The patient notes the lesion is flat and rough or flaky. No relevant systemic symptoms. Reported lesion symptoms include itching, enlargement and bothersome appearance. The subject is 60–69, female. The patient considered this a rash. Present for more than one year. The lesion involves the back of the torso, top or side of the foot, leg and arm. Close-up view — 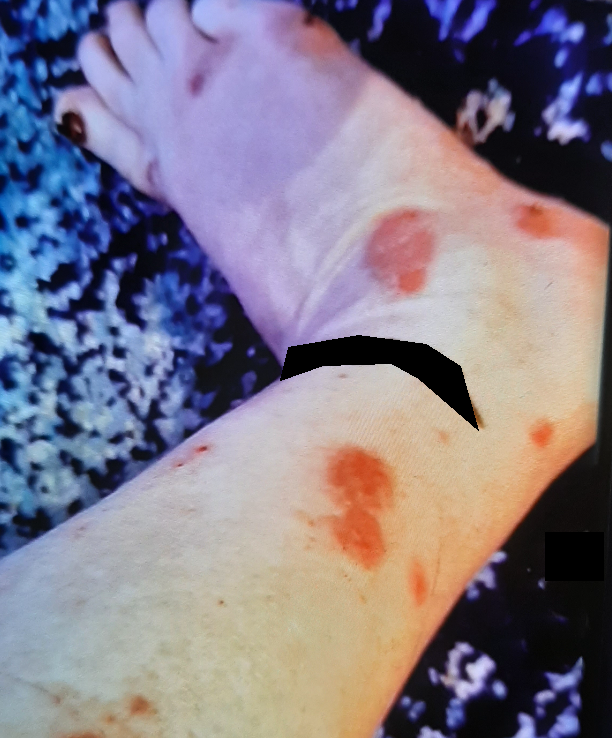<report>
  <differential>
    <leading>Bullous Pemphigoid</leading>
    <considered>Infected eczema</considered>
  </differential>
</report>